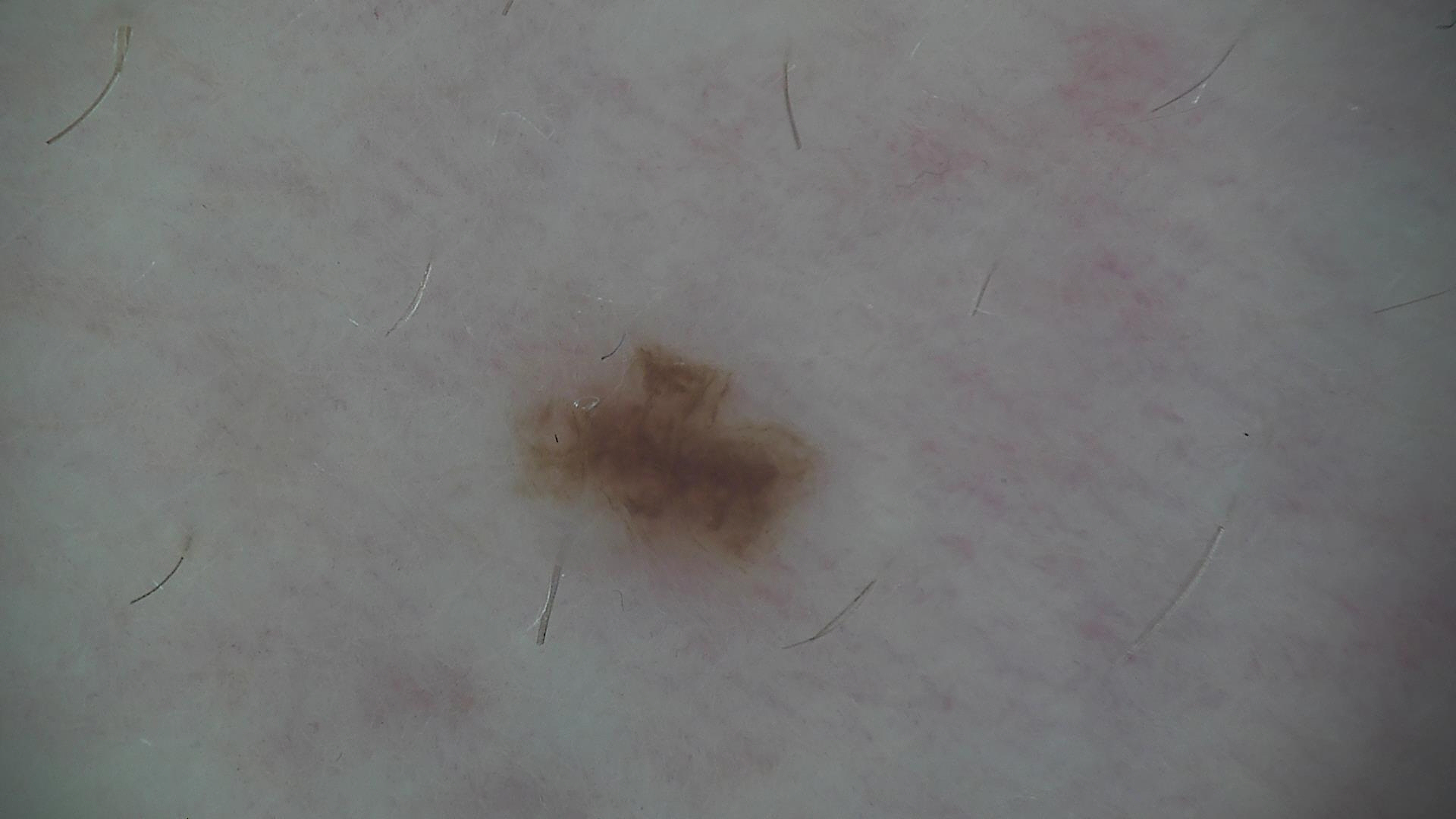diagnostic label = dysplastic junctional nevus (expert consensus).